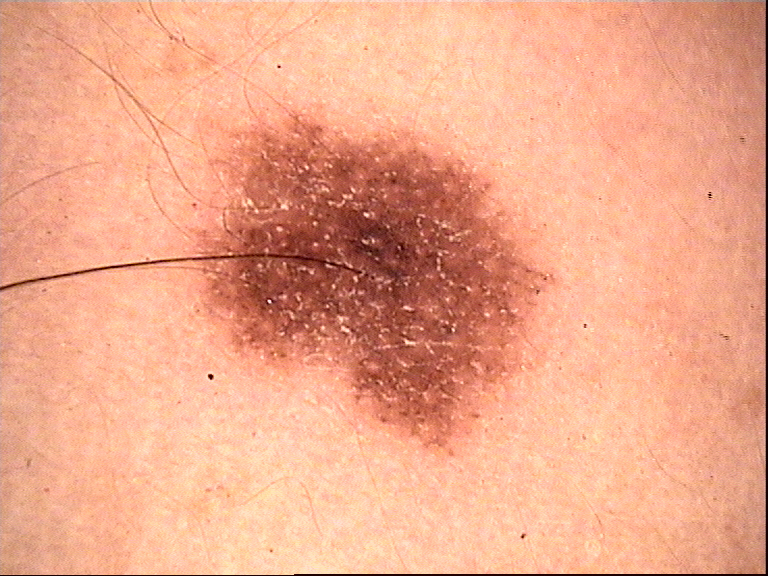Consistent with a dysplastic junctional nevus.